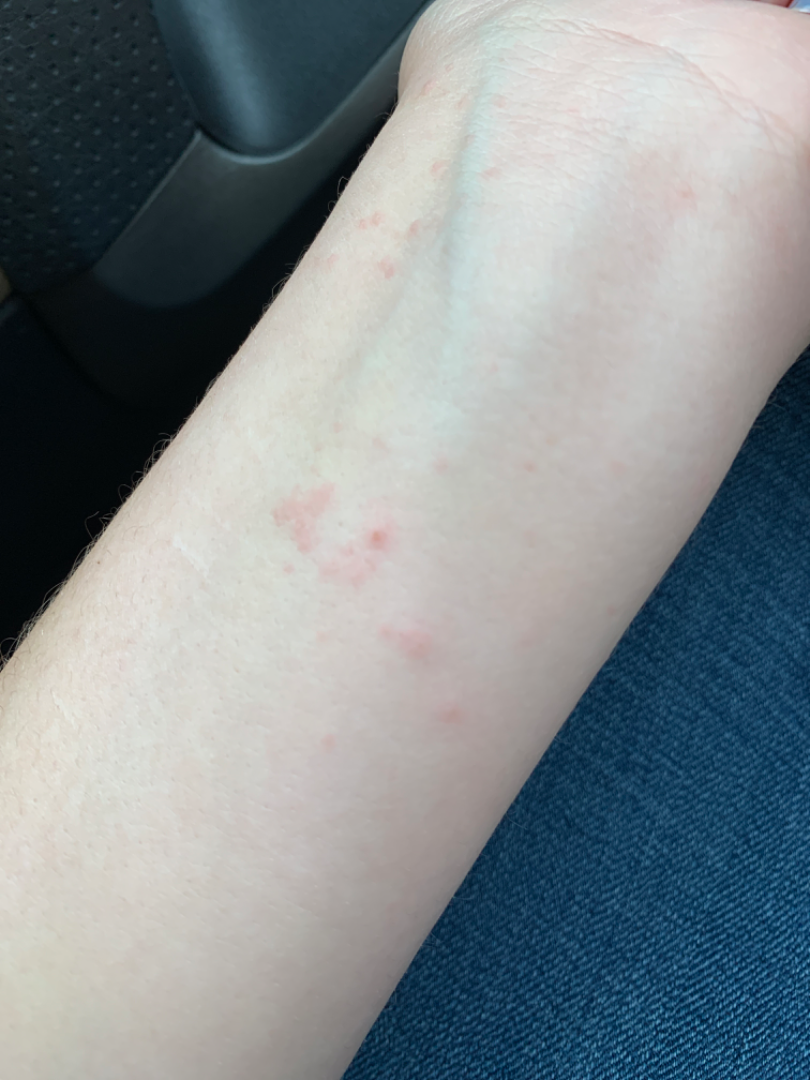lesion symptoms — itching | patient describes the issue as — a rash | affected area — arm | associated systemic symptoms — none reported | framing — at an angle | history — less than one week | dermatologist impression — single-reviewer assessment: favoring Allergic Contact Dermatitis; possibly Lichen planus/lichenoid eruption; an alternative is Eczema.